The patient says their skin tans without first burning. The patient describes having a moderate number of moles. By self-report, a personal history of cancer and a family history of skin cancer. A female subject age 64. The referring clinician suspected basal cell carcinoma. A clinical photograph showing a skin lesion — 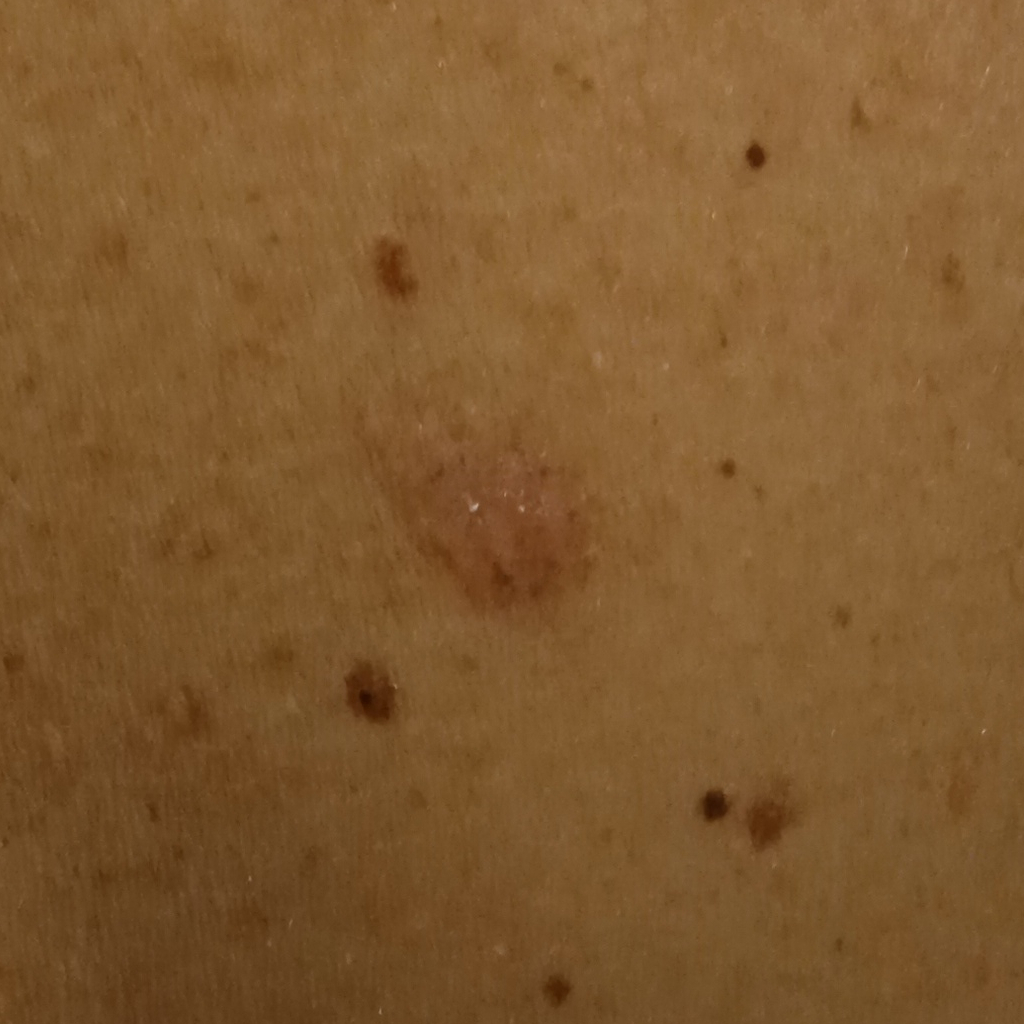The lesion is located on the back. The lesion is about 9.8 mm across. The biopsy diagnosis was a basal cell carcinoma, following excision, with tumor thickness 1 mm.